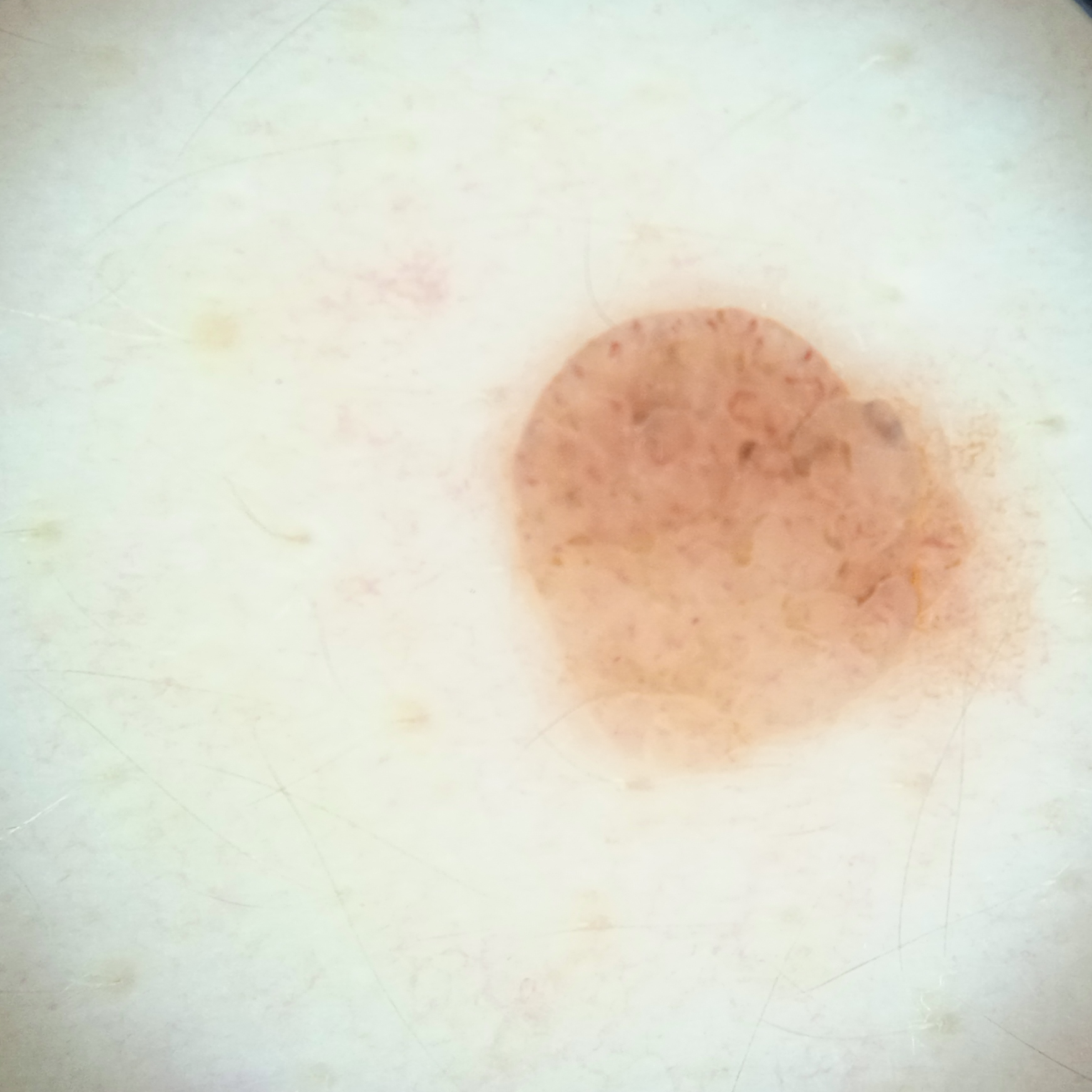nevus count = numerous melanocytic nevi
patient = female, 26 years of age
relevant history = a history of sunbed use
sun reaction = skin reddens with sun exposure
modality = dermoscopy
referral context = research study (no referral diagnosis)
assessment = melanocytic nevus (dermatologist consensus)